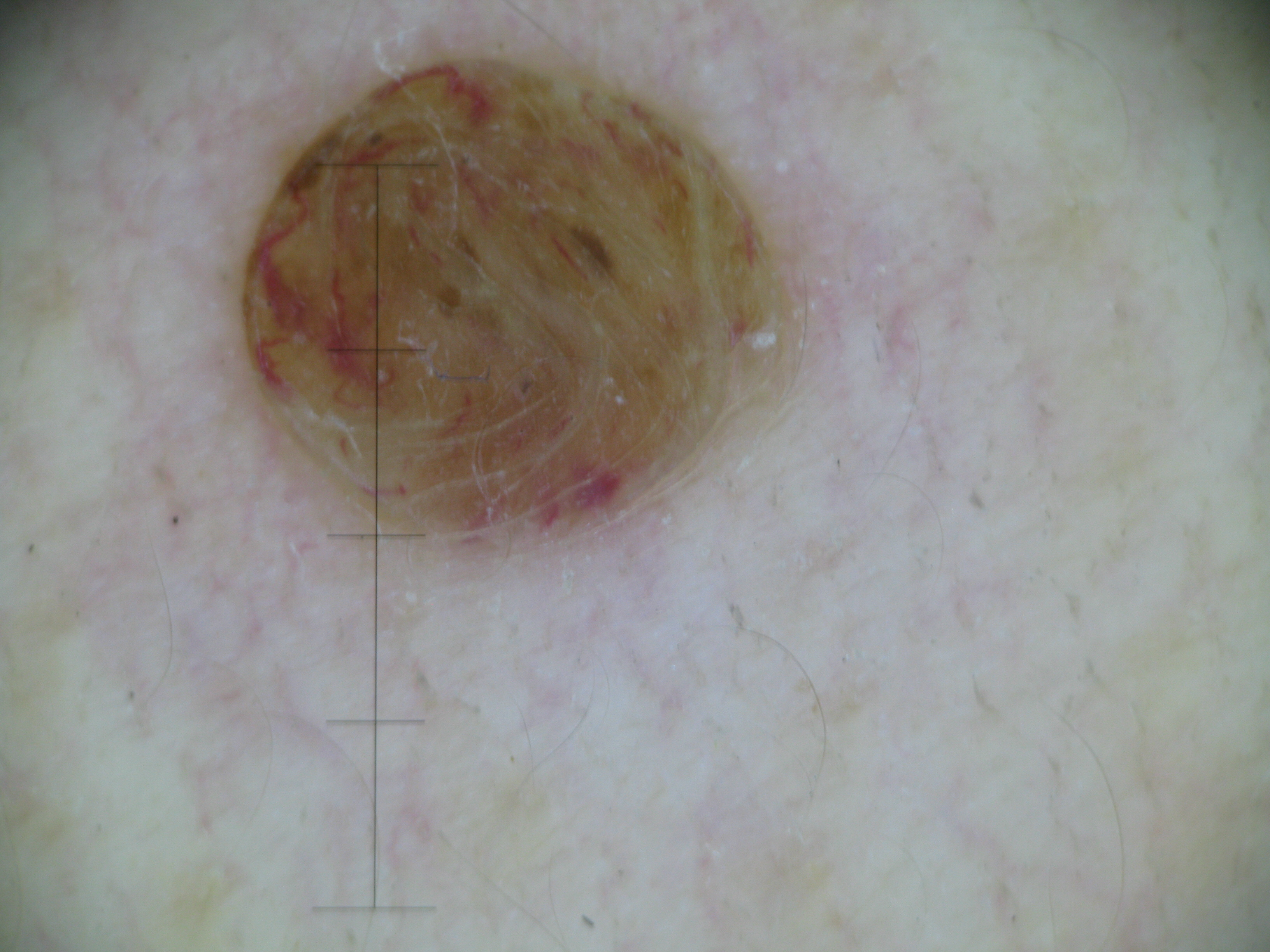Case:
A dermoscopic close-up of a skin lesion. The architecture is that of a banal lesion.
Impression:
Diagnosed as a dermal nevus.